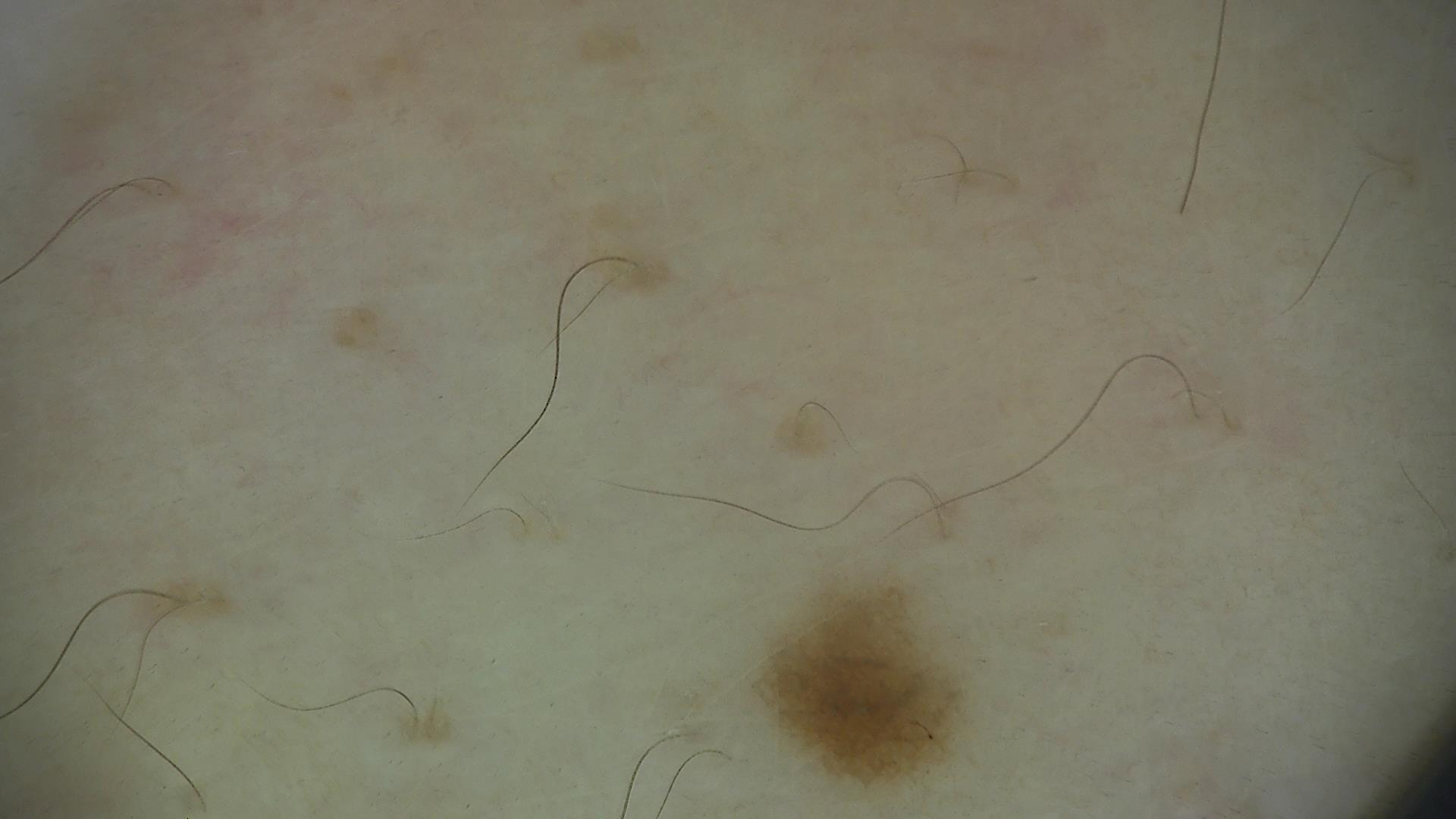A dermoscopy image of a single skin lesion. The diagnostic label was a dysplastic junctional nevus.